Imaged for a research study, with no referral diagnosis recorded; numerous moles by the patient's own estimate; on a questionnaire the patient reported a history of sunbed use, no immunosuppression, and no personal history of cancer; a female subject aged 26: 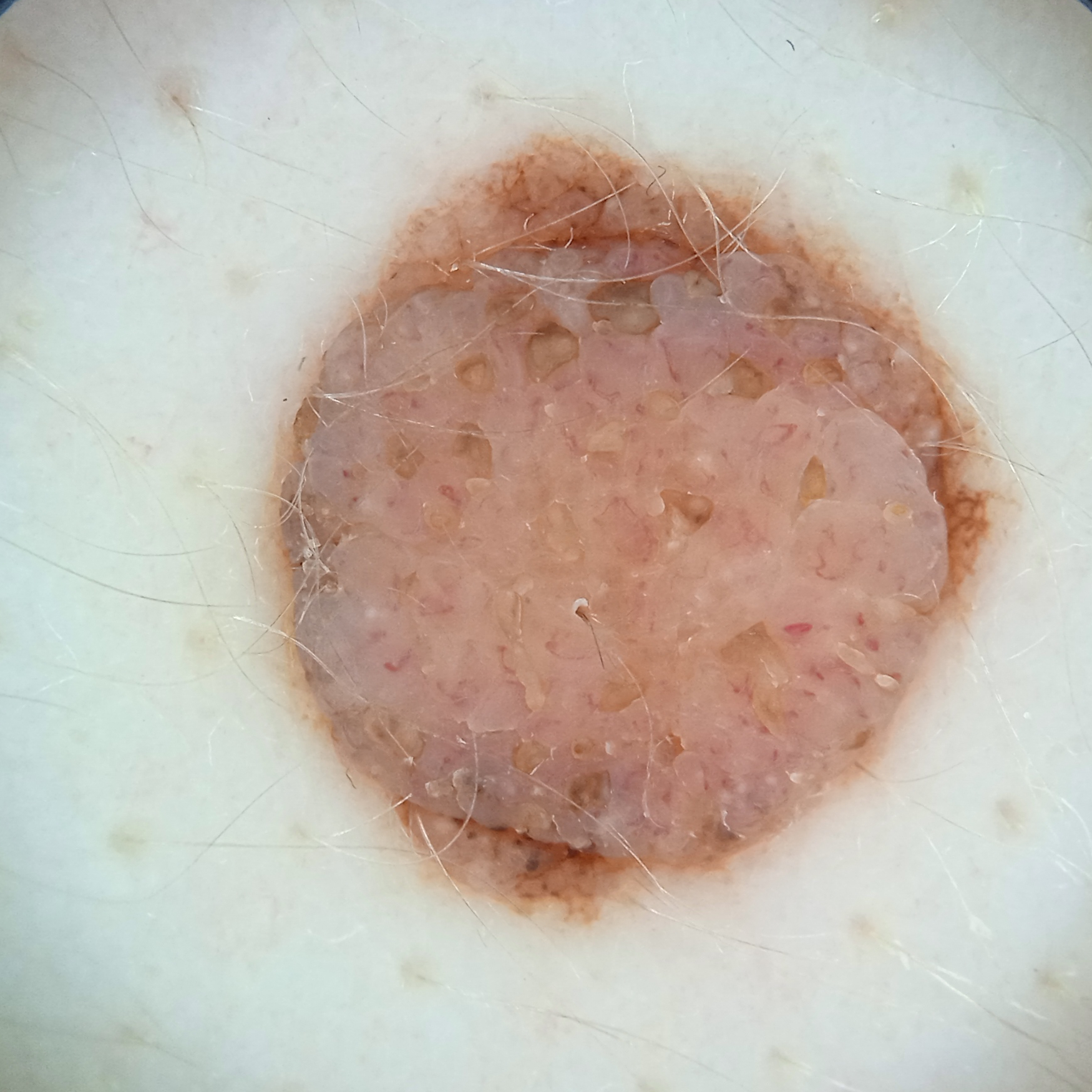{"lesion_location": "the back", "lesion_size": {"diameter_mm": 8.9}, "diagnosis": {"name": "melanocytic nevus", "malignancy": "benign"}}